A subject in their mid-50s. A clinical photograph of a skin lesion: 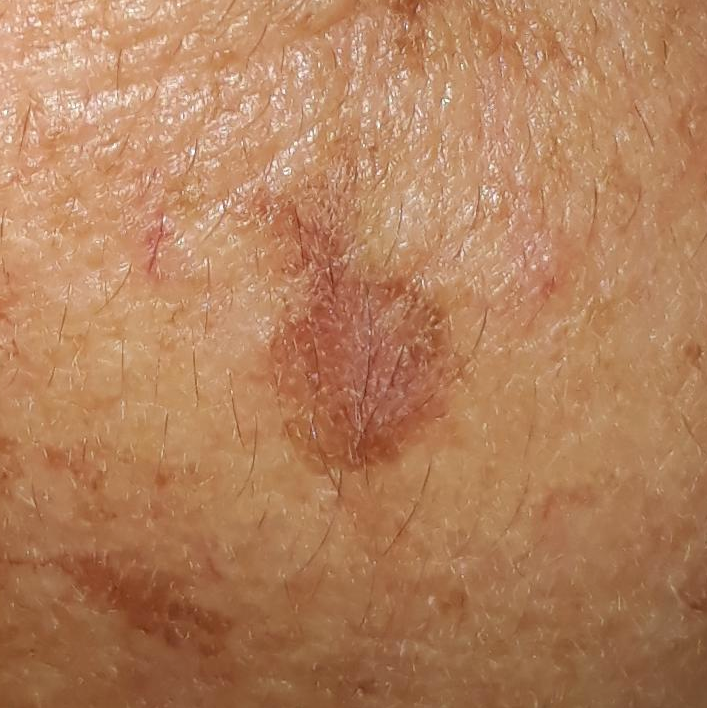anatomic site=the face
symptoms=growth
assessment=nevus (clinical consensus)